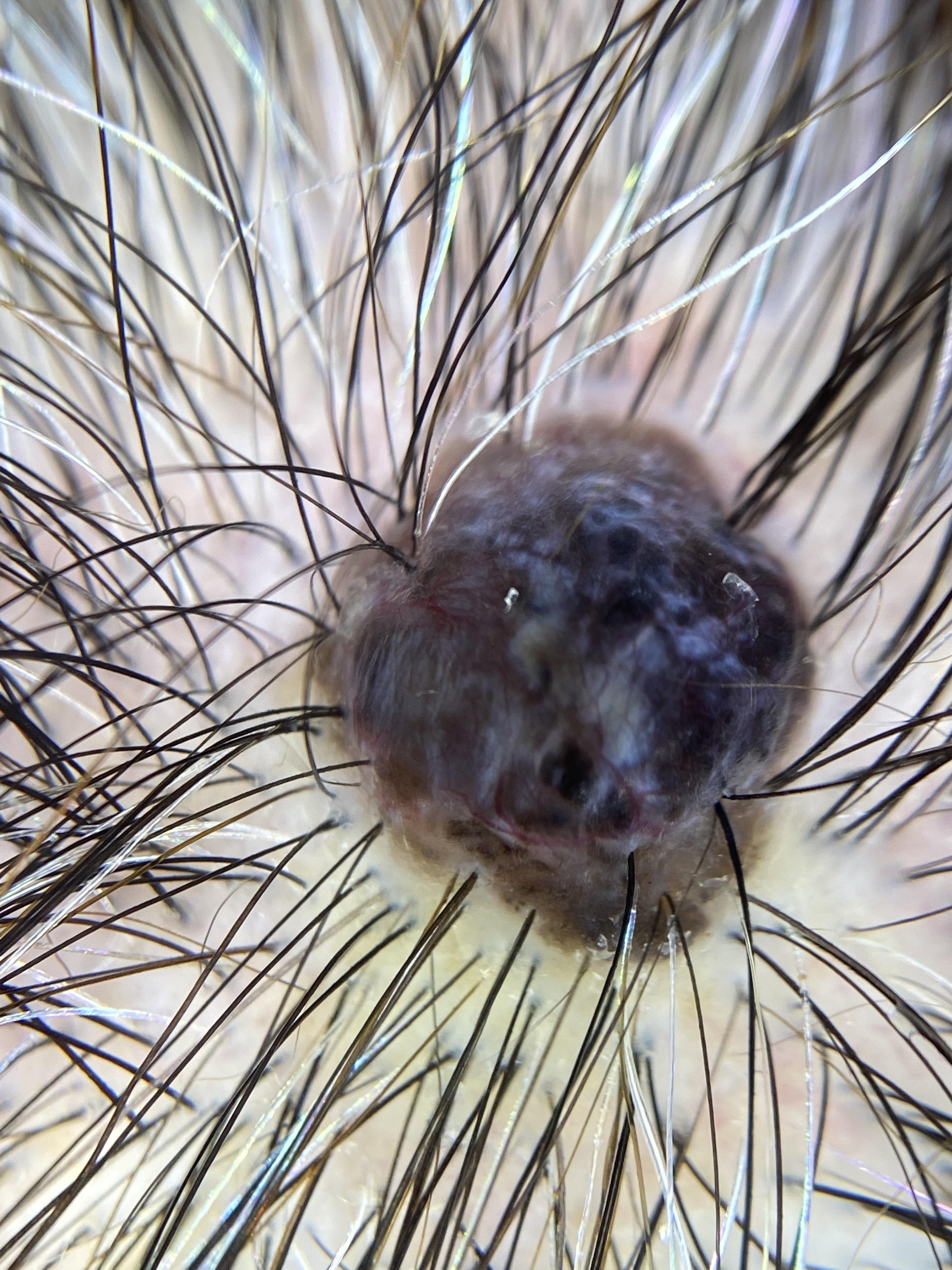{
  "patient": {
    "age_approx": 45,
    "sex": "female"
  },
  "lesion_location": {
    "region": "the head or neck"
  },
  "diagnosis": {
    "name": "Basal cell carcinoma",
    "malignancy": "malignant",
    "confirmation": "histopathology",
    "lineage": "adnexal"
  }
}